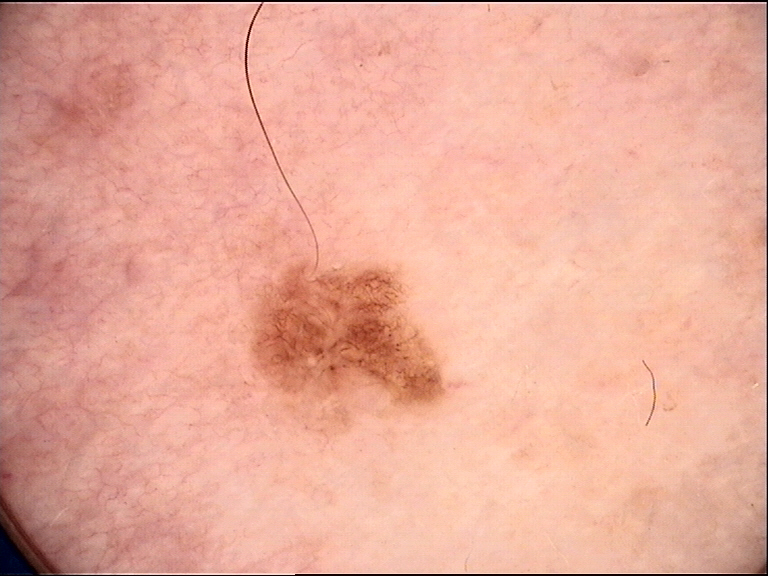Q: What is this lesion?
A: dysplastic junctional nevus (expert consensus)